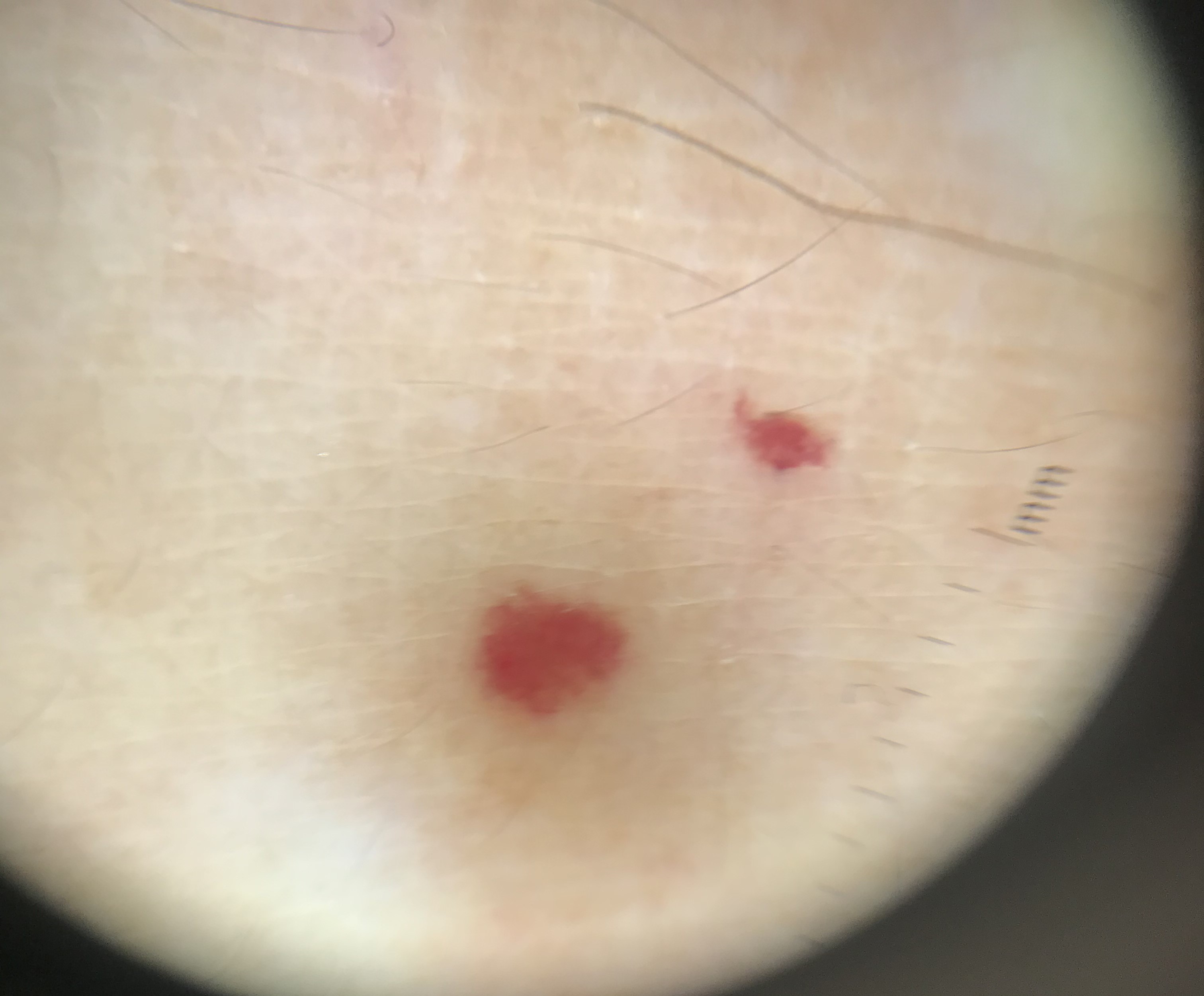Case:
Dermoscopy of a skin lesion. The morphology is that of a vascular lesion.
Impression:
Consistent with a hemangioma.